Dermoscopy of a skin lesion: 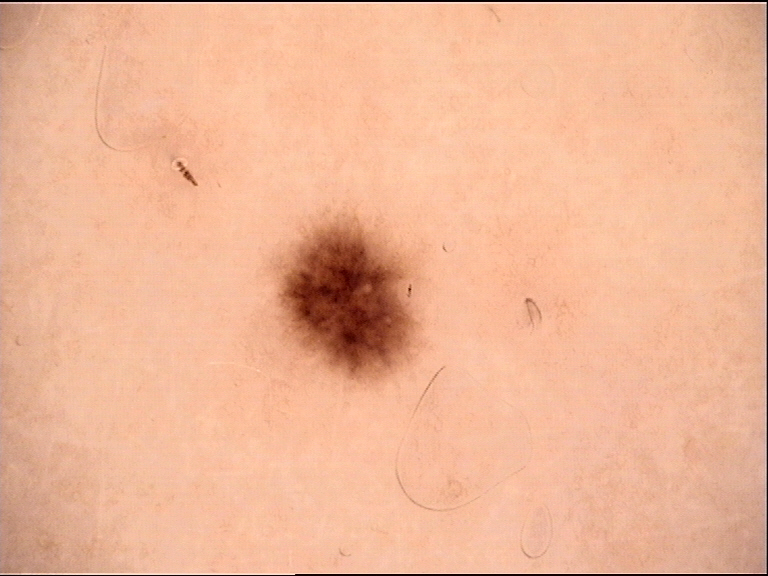Case:
* classification: banal
* label: junctional nevus (expert consensus)